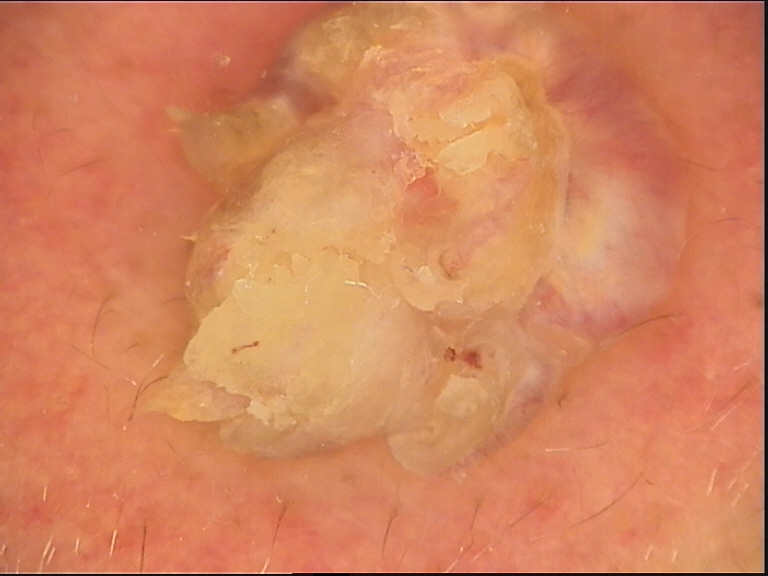Diagnosis:
Biopsy-confirmed as a keratinocytic lesion — a squamous cell carcinoma.